The patient describes having a moderate number of moles · dermoscopy of a skin lesion · acquired for a research image collection, with no referral diagnosis · the patient says their skin reddens painfully with sun exposure · a female patient 81 years of age:
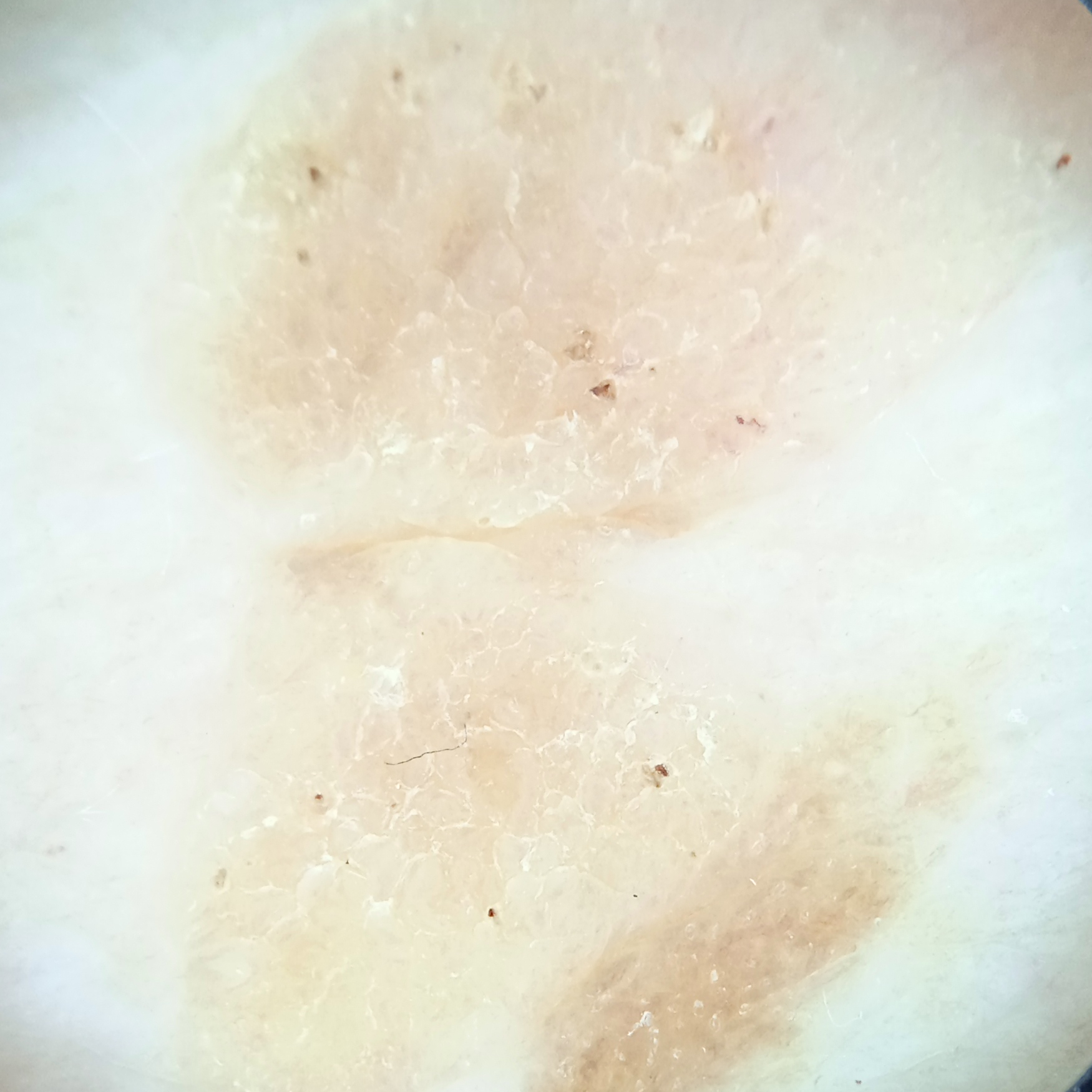Located on the back. The lesion is about 15.5 mm across. The diagnostic impression was a seborrheic keratosis.